Dermoscopy of a skin lesion, the patient is a female about 15 years old:
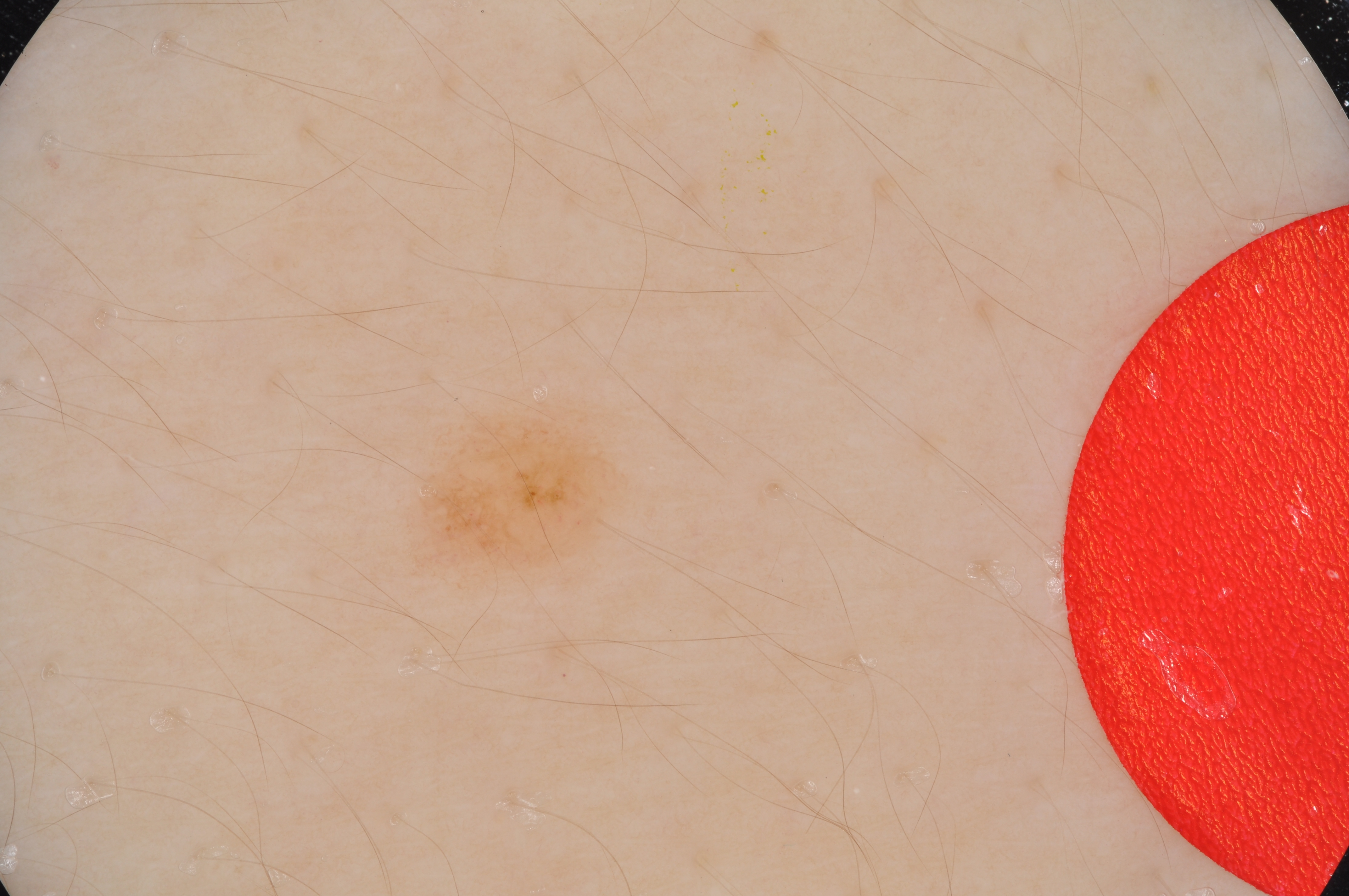size=small | bounding box=[390, 397, 629, 601] | features=pigment network; absent: streaks, milia-like cysts, globules, and negative network | impression=a melanocytic nevus, a benign lesion.